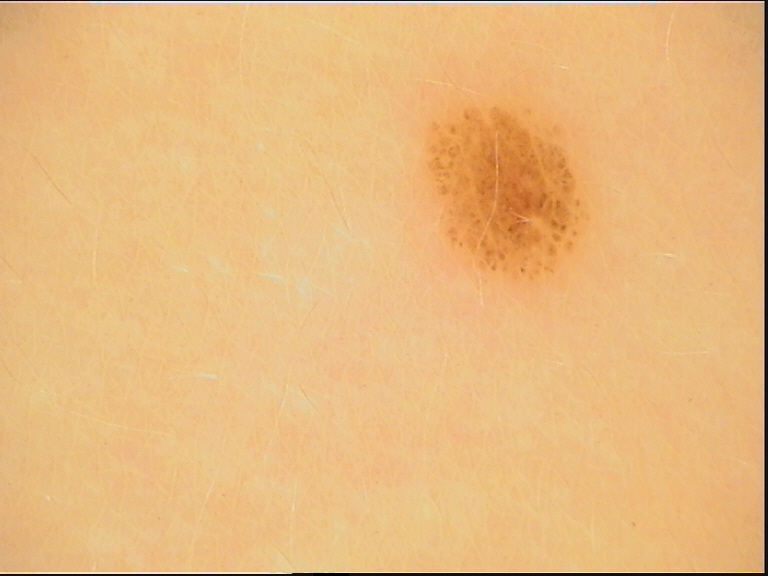Impression:
Classified as a dysplastic junctional nevus.